A male subject approximately 85 years of age or older · a clinical overview photograph of a skin lesion · Fitzpatrick II: 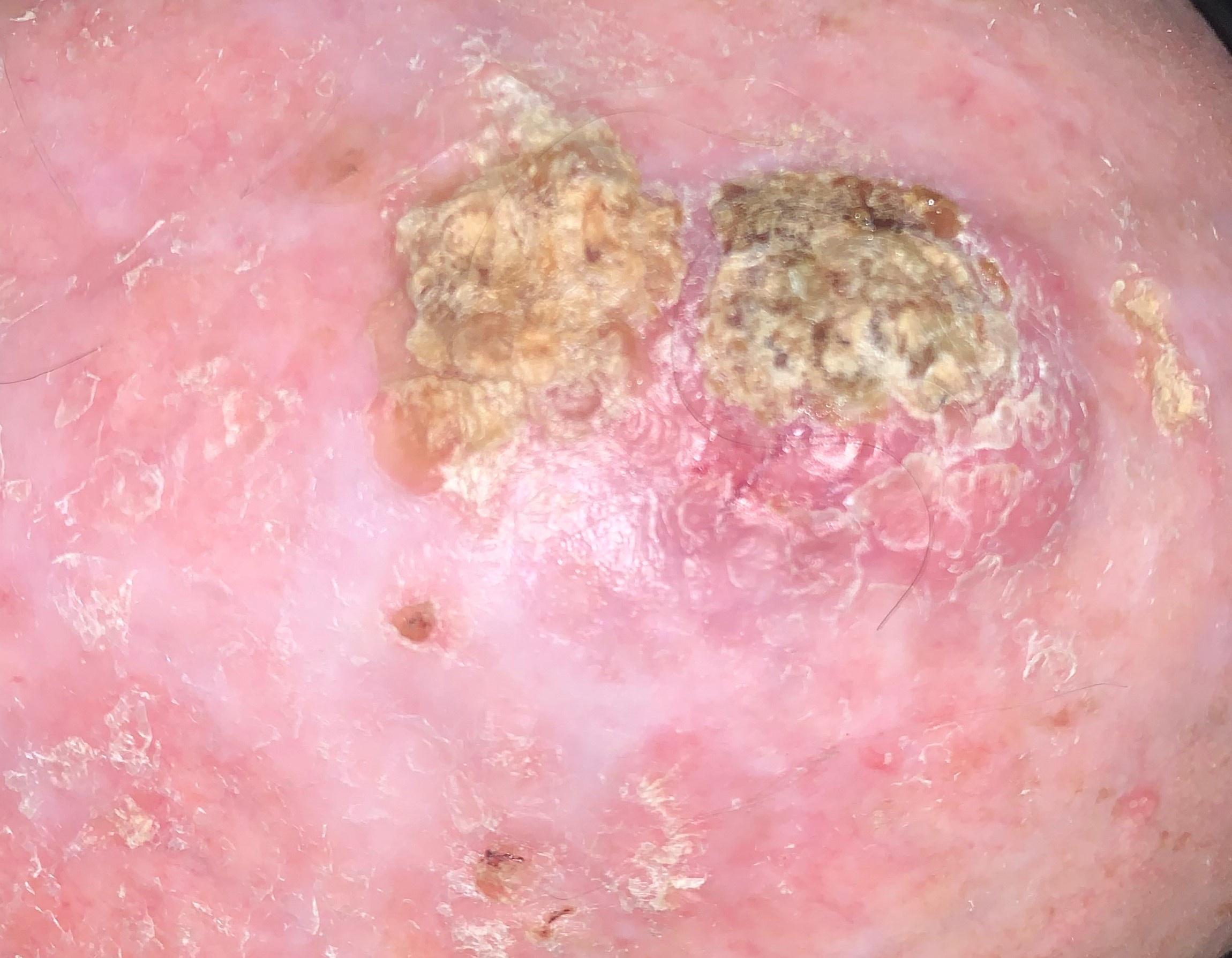The lesion is on the head or neck. Histopathology confirmed a squamous cell carcinoma.